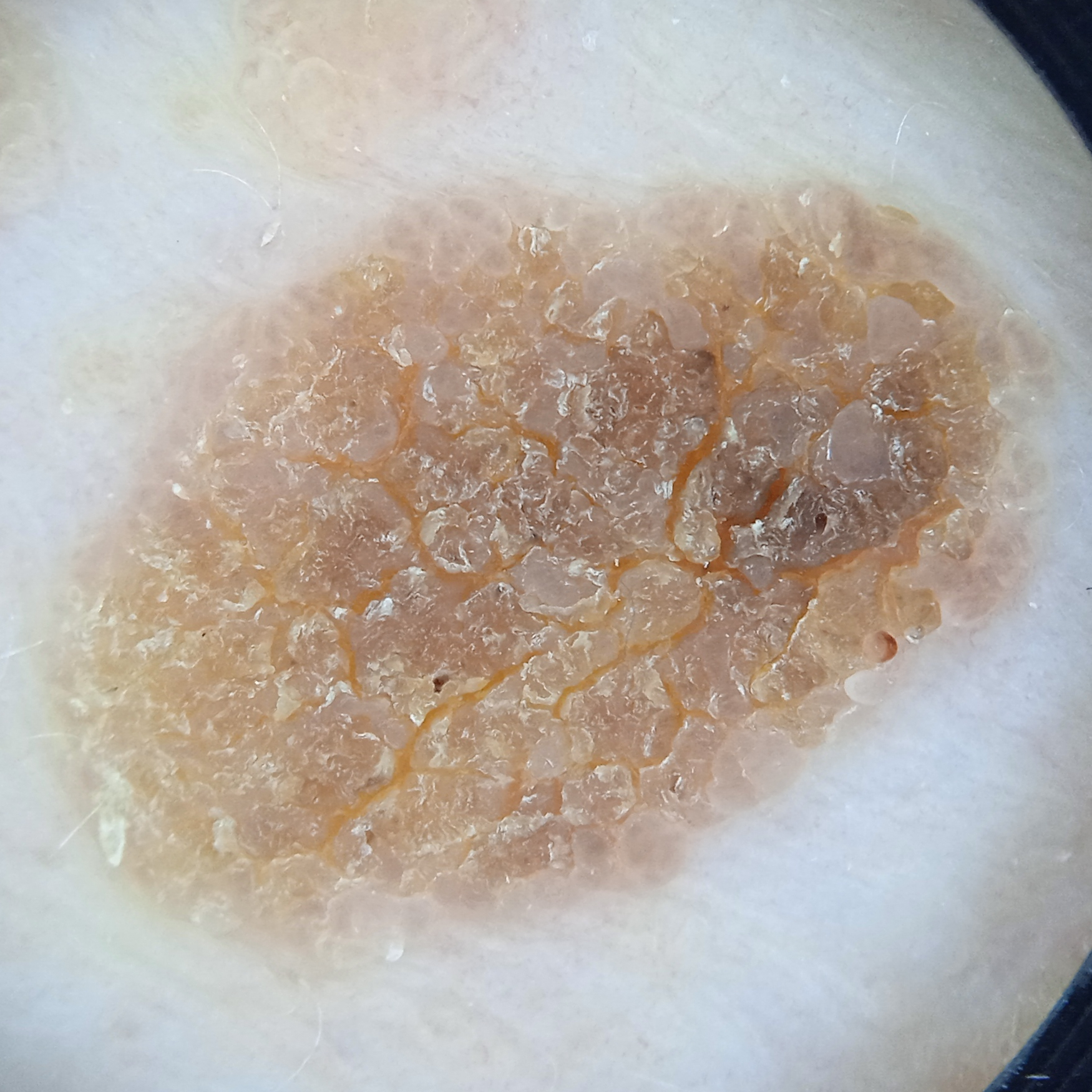diagnosis:
  name: seborrheic keratosis
  malignancy: benign